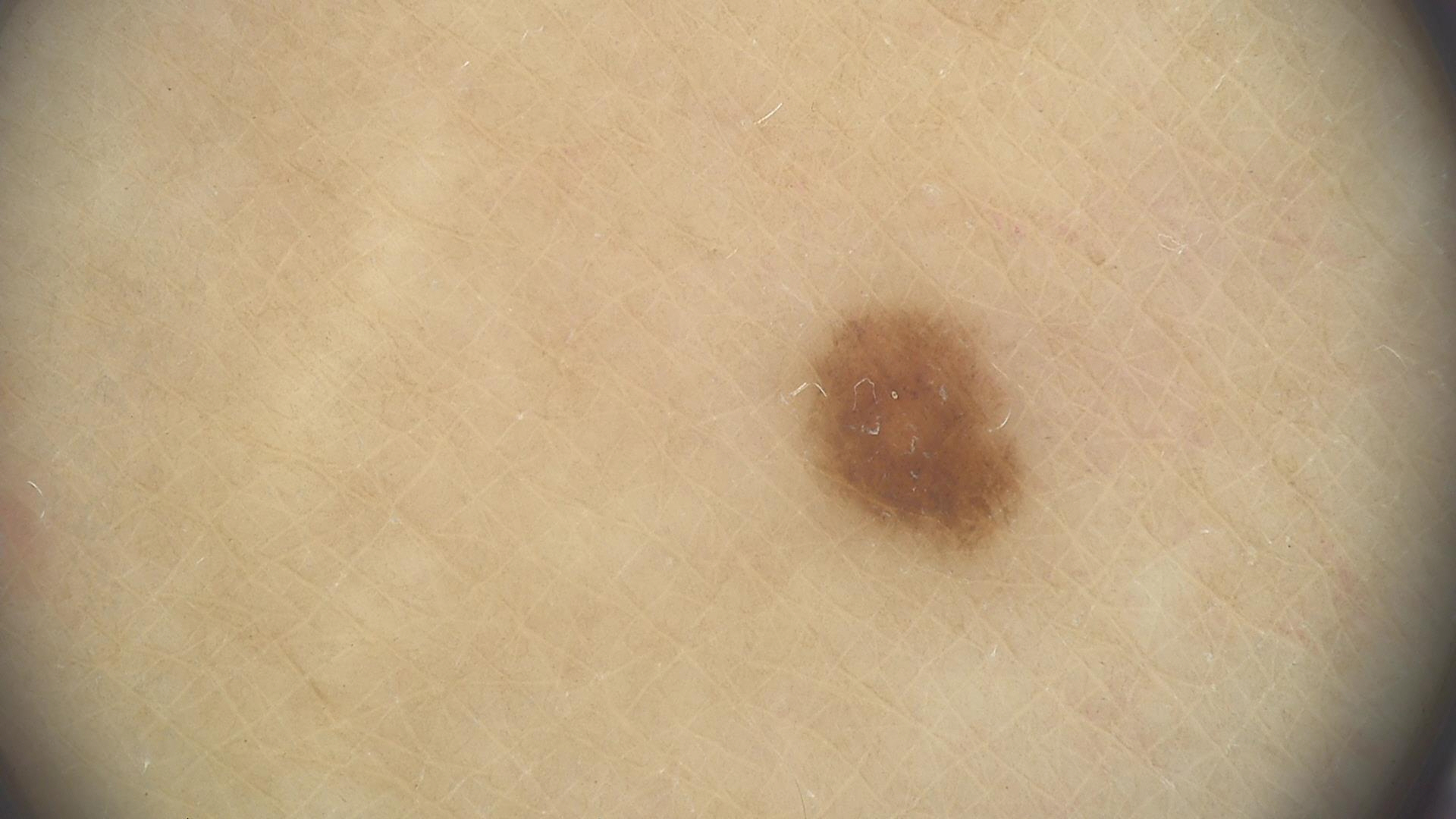Findings:
A dermatoscopic image of a skin lesion.
Impression:
Labeled as a banal lesion — a junctional nevus.